The lesion involves the head or neck, front of the torso, arm and leg · this image was taken at an angle: 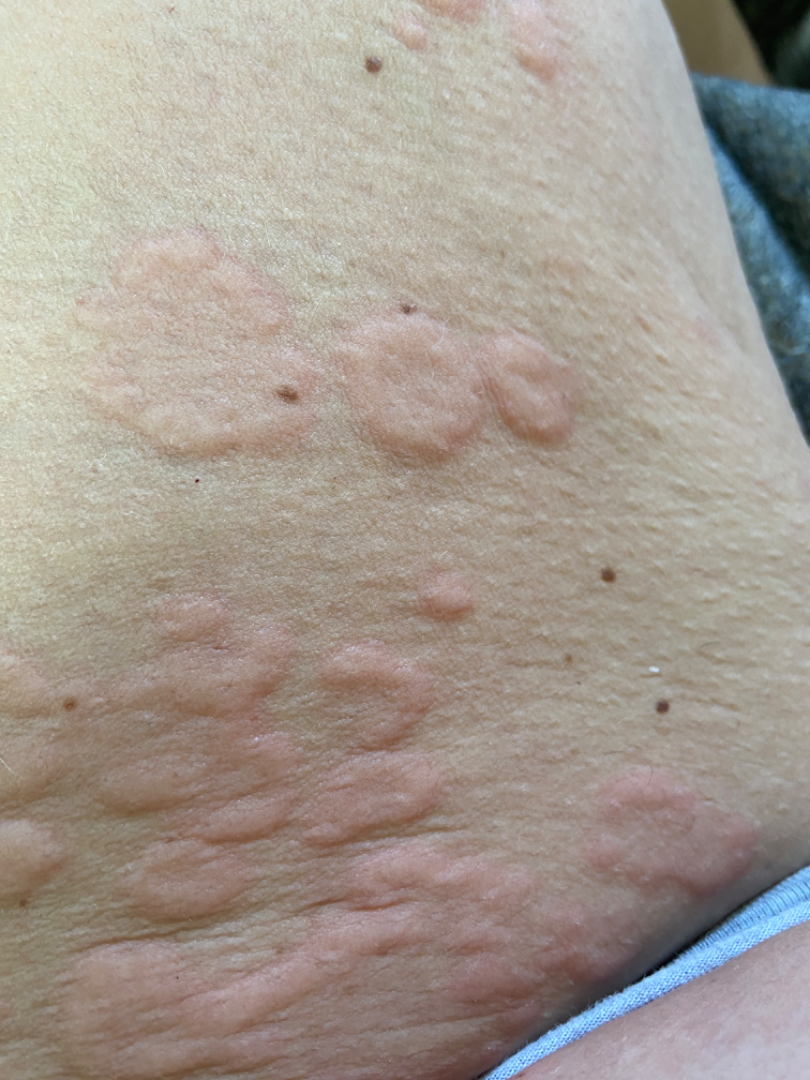History:
The patient considered this a rash. The lesion is described as raised or bumpy. The patient reports associated fatigue. Present for less than one week. Symptoms reported: enlargement, bothersome appearance and itching.
Impression:
On remote review of the image: in keeping with Urticaria.